This image was taken at an angle:
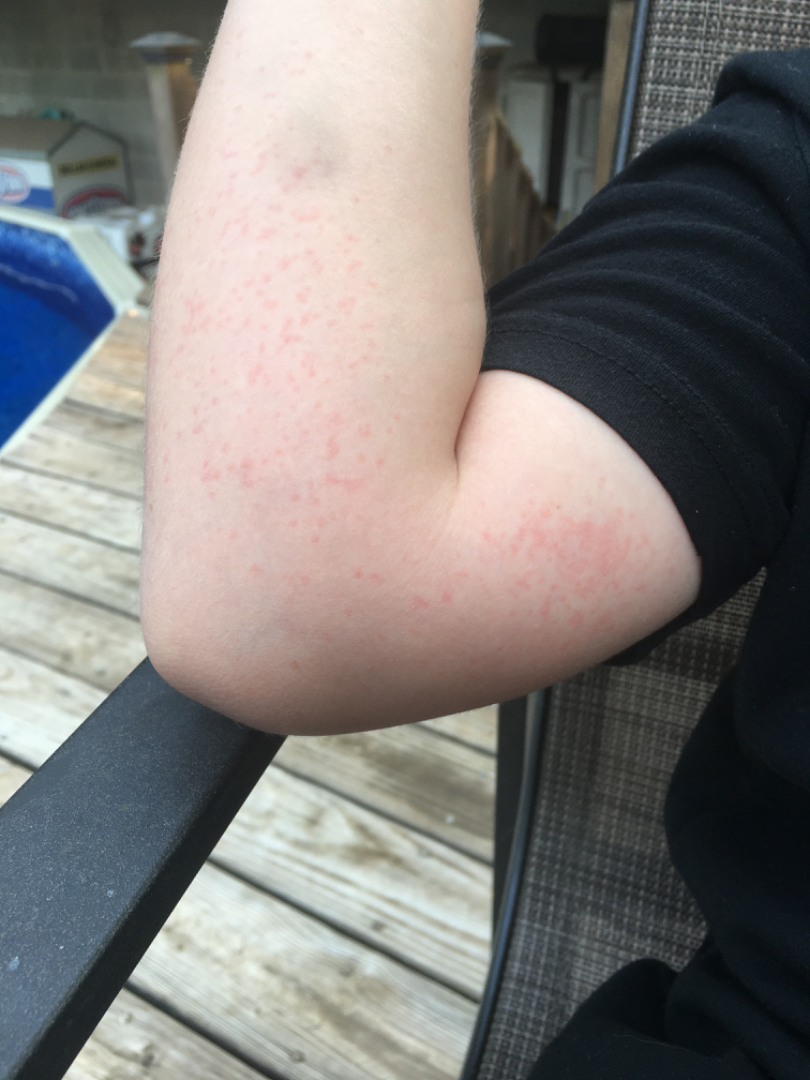Assessment: The condition could not be reliably identified from the image.